This is a close-up image: 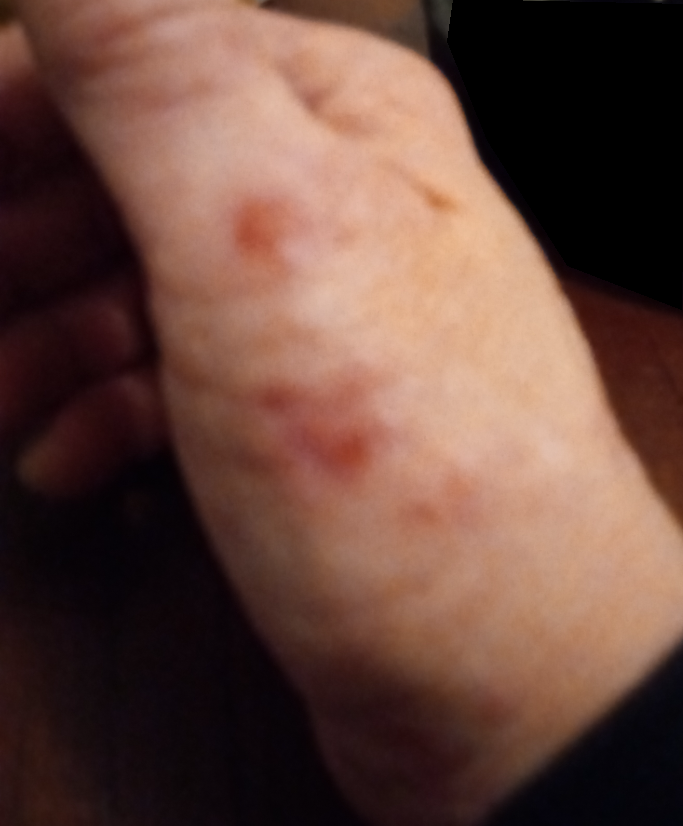No differential diagnosis could be assigned on photographic review.